Close-up view · located on the arm, back of the torso and leg:
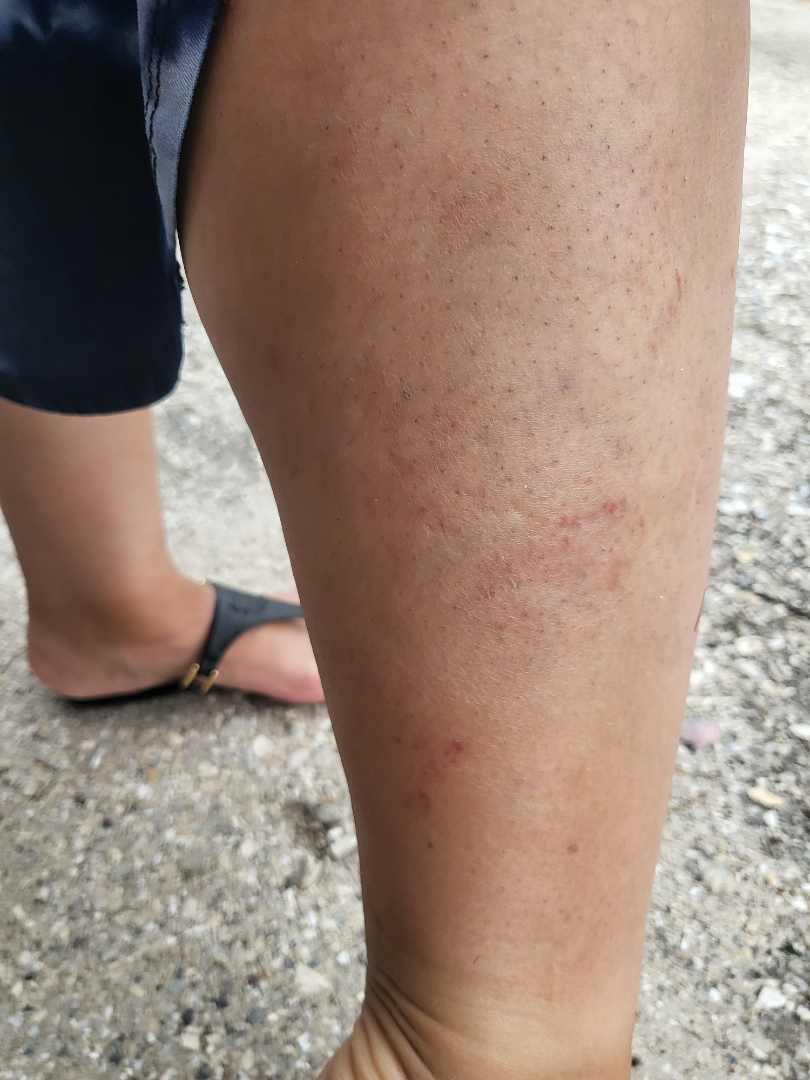<summary>
  <assessment>could not be assessed</assessment>
</summary>